A dermoscopic image of a skin lesion:
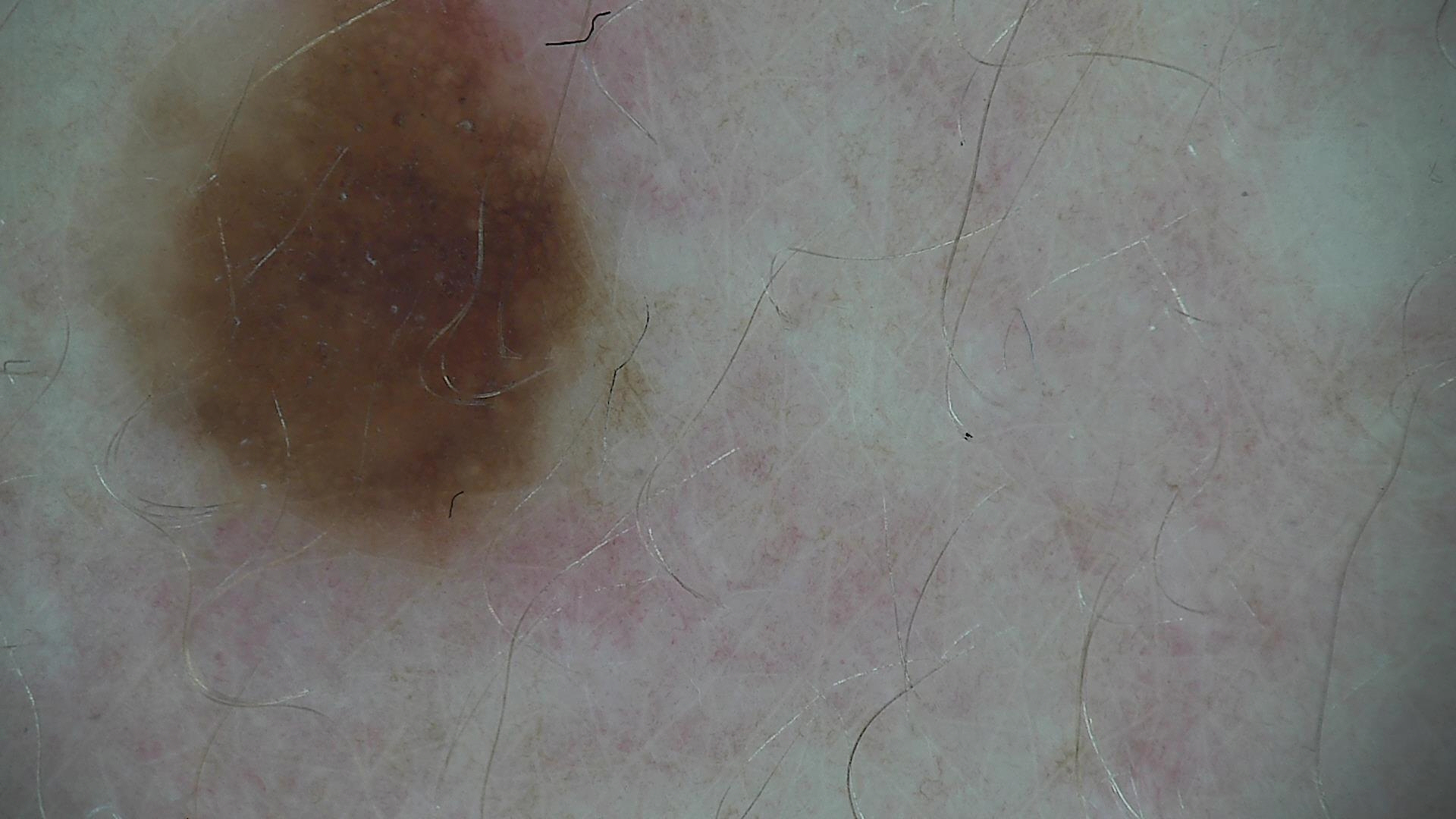diagnosis: dysplastic compound nevus (expert consensus).